Self-categorized by the patient as a rash · FST II; human graders estimated 3 on the MST · no associated systemic symptoms reported · reported lesion symptoms include burning, enlargement and itching · located on the back of the hand · close-up view · the condition has been present for less than one week:
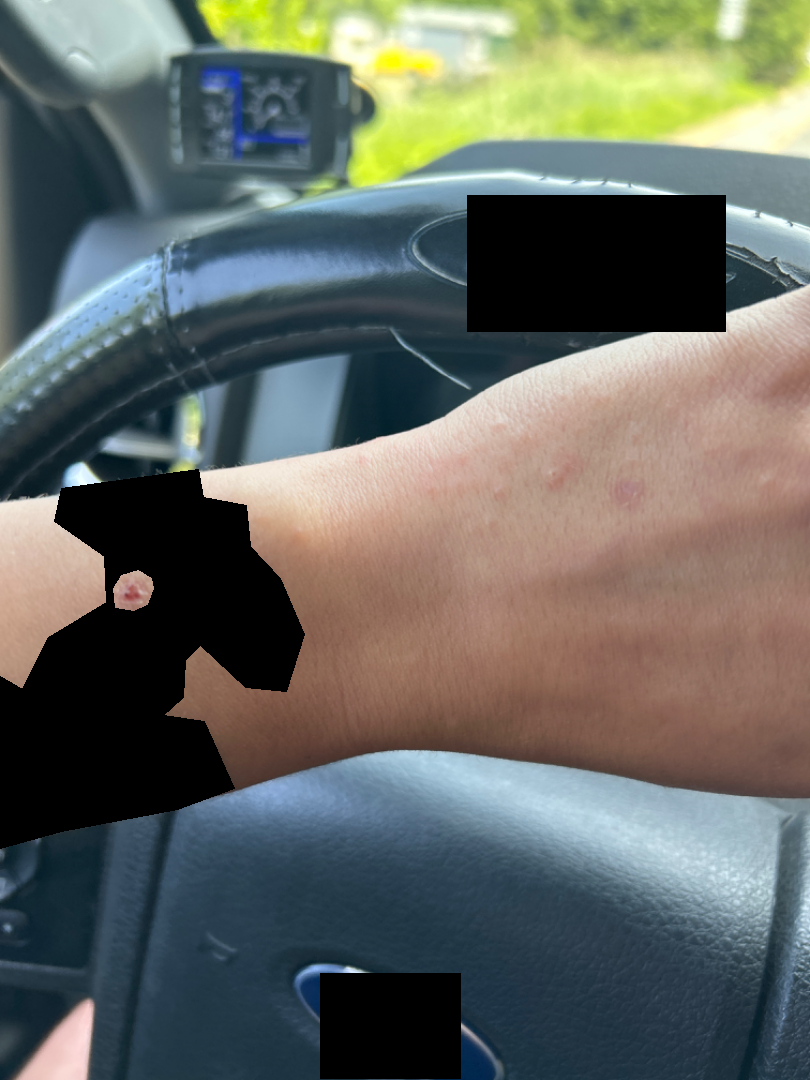Q: Could the case be diagnosed?
A: ungradable on photographic review